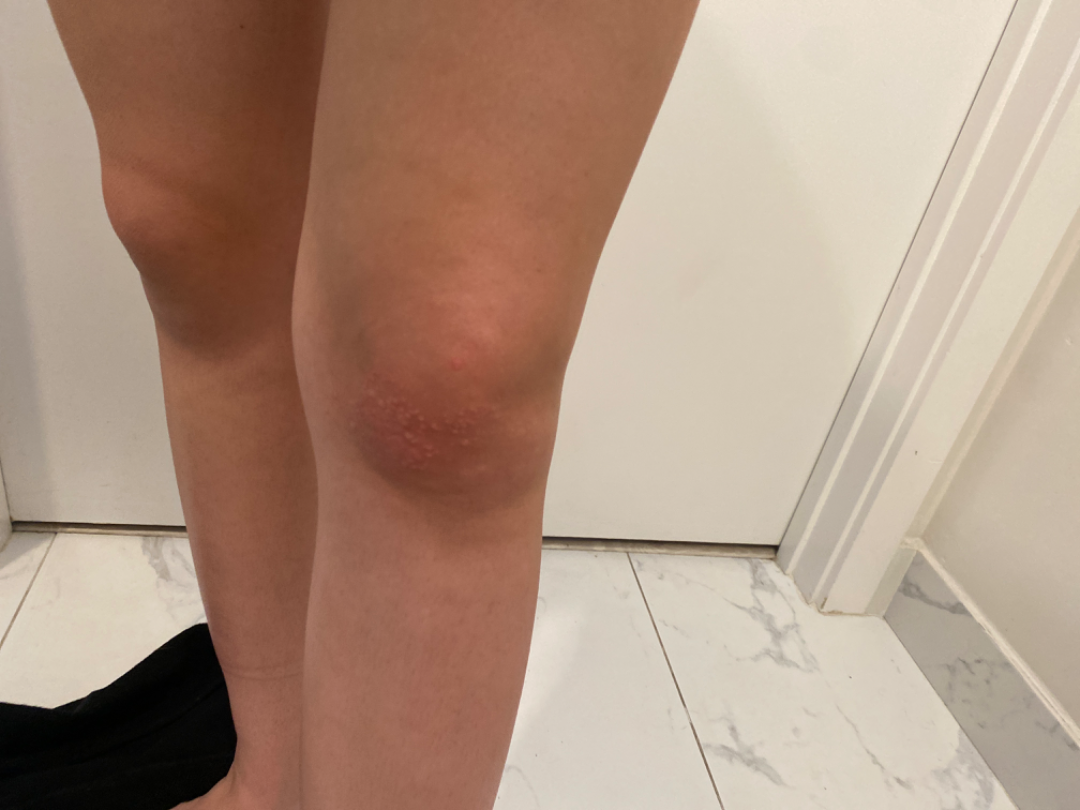Texture is reported as raised or bumpy. No relevant systemic symptoms. The condition has been present for one to three months. The patient is a female aged 18–29. The affected area is the leg and arm. An image taken at a distance. The contributor notes enlargement, bothersome appearance and itching. On remote dermatologist review, most consistent with Allergic Contact Dermatitis; also consider Herpes Zoster; with consideration of Herpes Simplex.